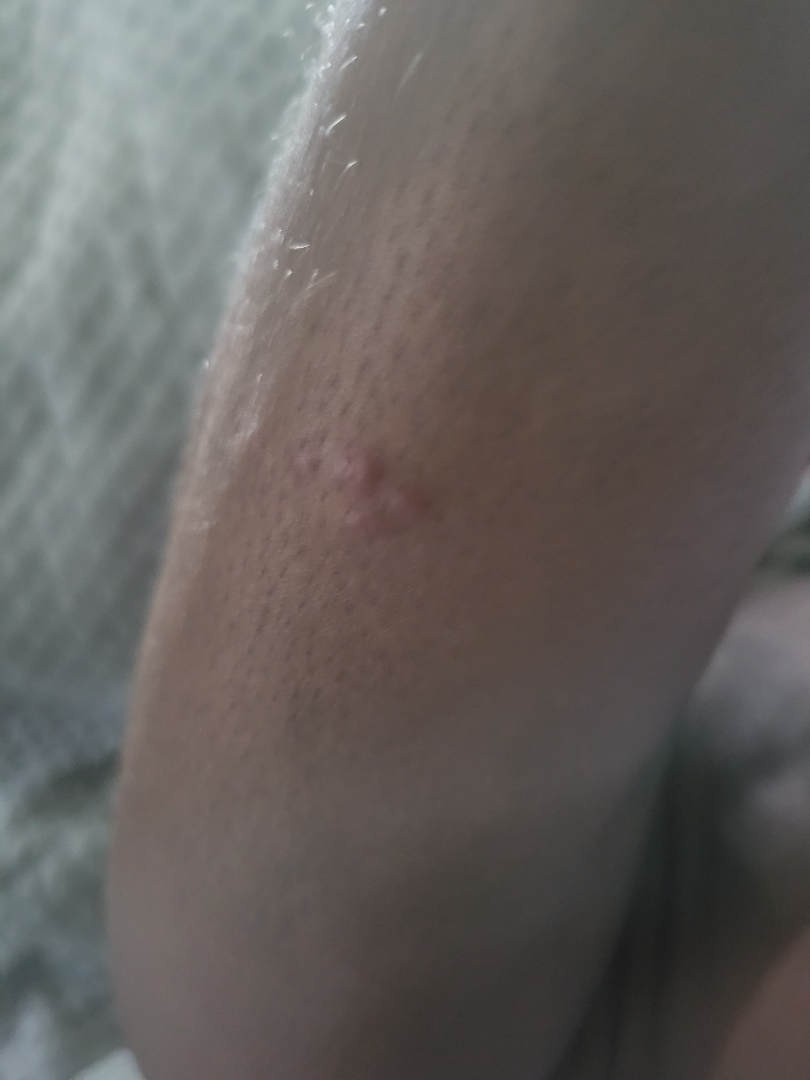- assessment · ungradable on photographic review
- onset · about one day
- photo taken · at a distance
- contributor · male, age 30–39
- self-categorized as · a rash
- reported symptoms · itching